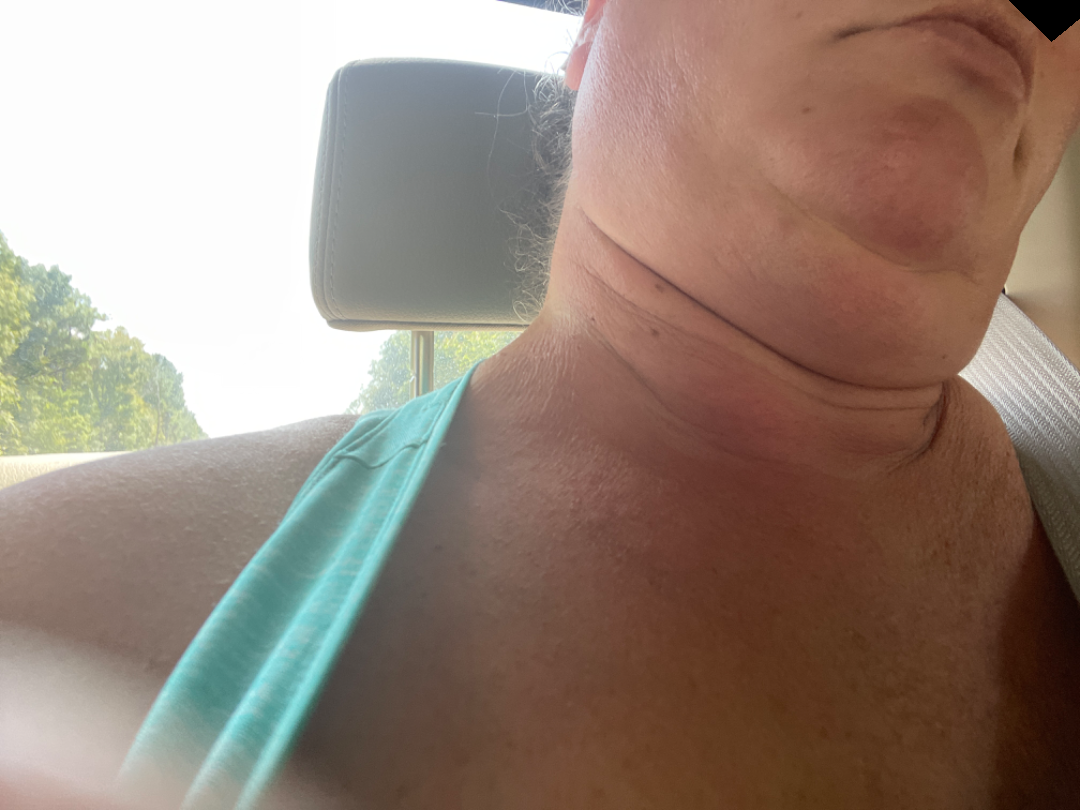assessment=could not be assessed; framing=close-up; site=head or neck.